Dermoscopy of a skin lesion.
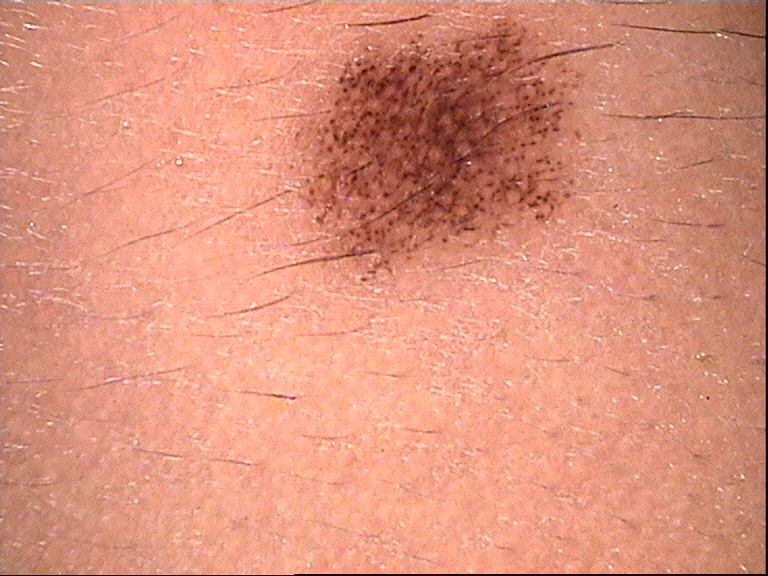Consistent with a dysplastic junctional nevus.